The patient is a female aged approximately 60; a dermoscopic view of a skin lesion: 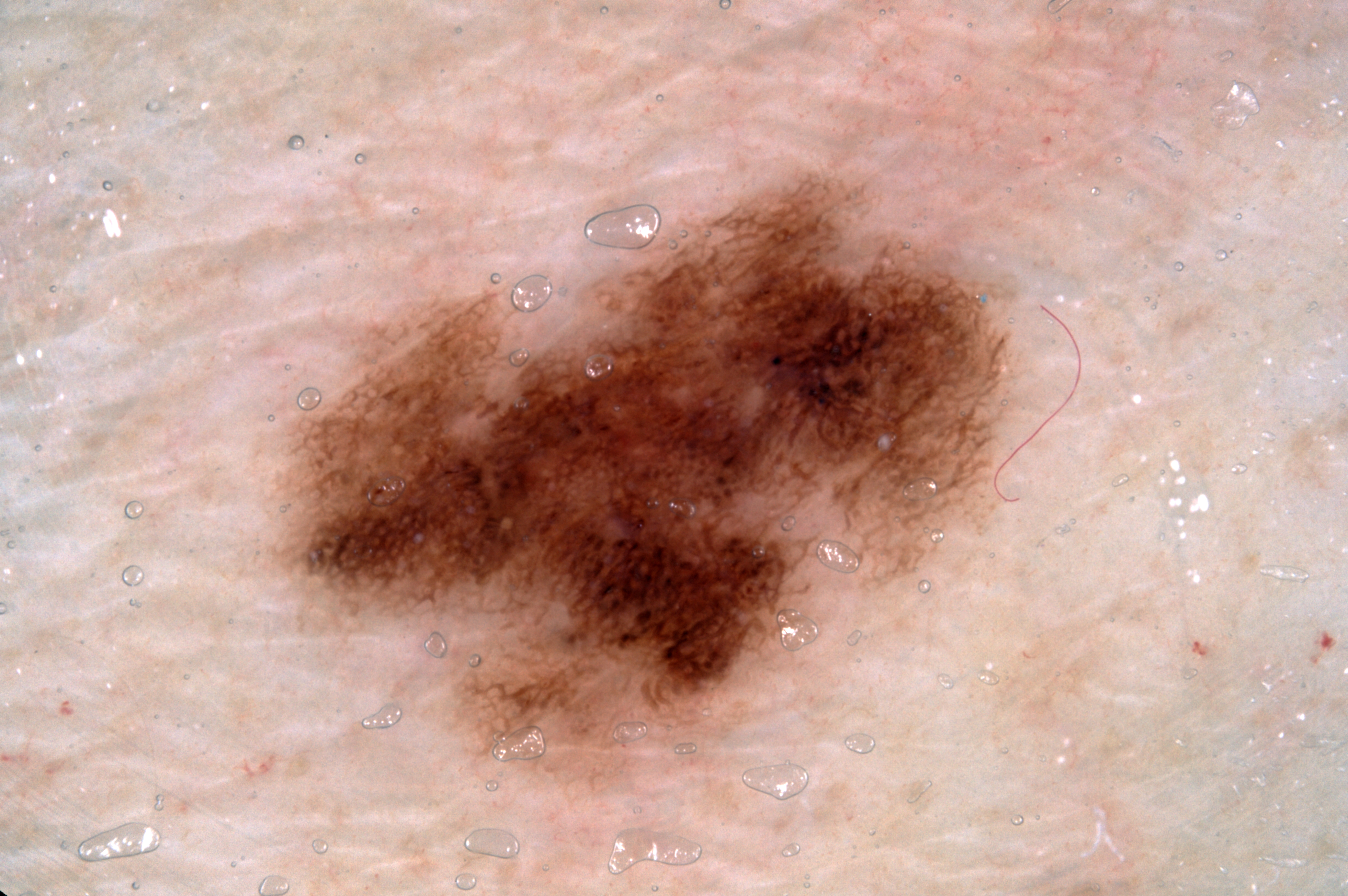Findings:
Dermoscopically, the lesion shows pigment network. The lesion occupies roughly 21% of the field. With coordinates (x1, y1, x2, y2), the lesion spans bbox=[295, 182, 1011, 770].
Assessment:
The clinical diagnosis was a melanocytic nevus, a benign lesion.